A dermatoscopic image of a skin lesion: 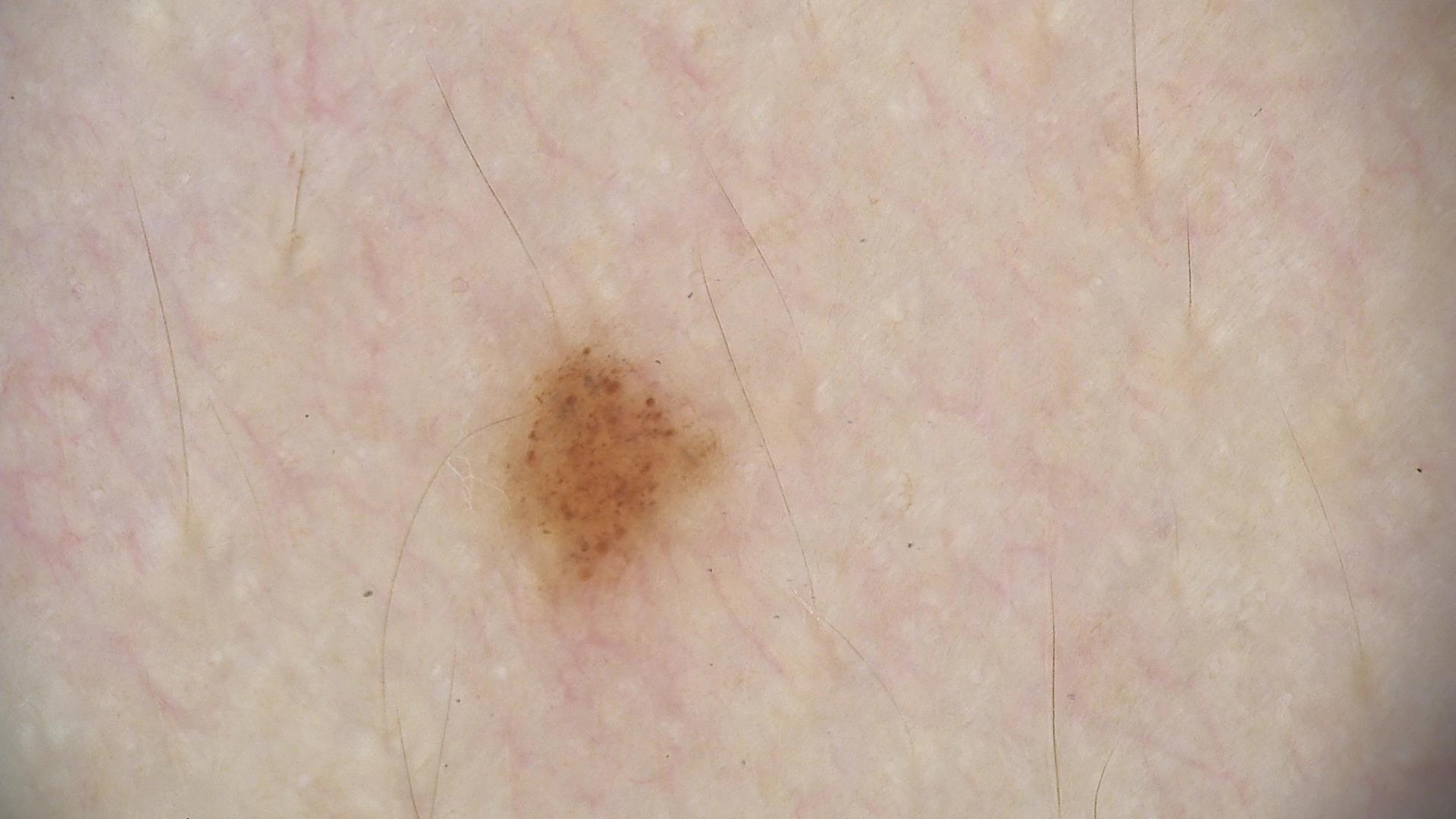This is a banal lesion. The diagnostic label was a junctional nevus.